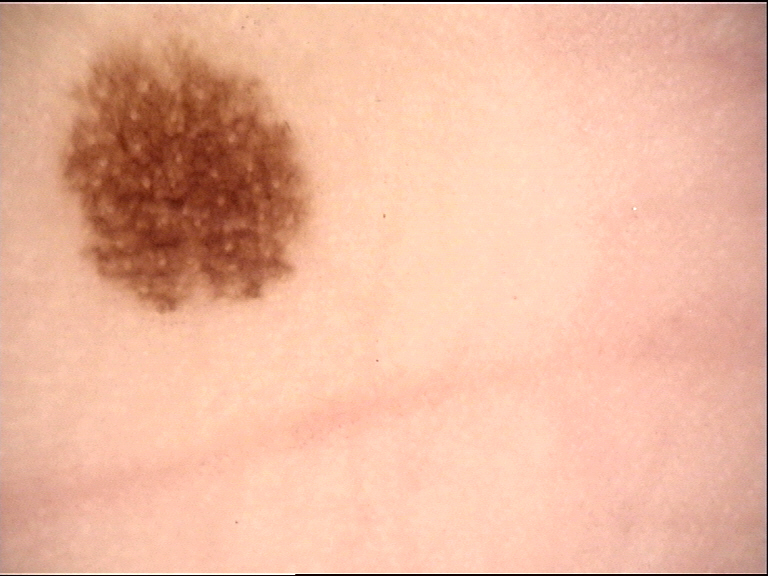<case>
  <image>dermatoscopy</image>
  <diagnosis>
    <name>acral dysplastic junctional nevus</name>
    <code>ajd</code>
    <malignancy>benign</malignancy>
    <super_class>melanocytic</super_class>
    <confirmation>expert consensus</confirmation>
  </diagnosis>
</case>